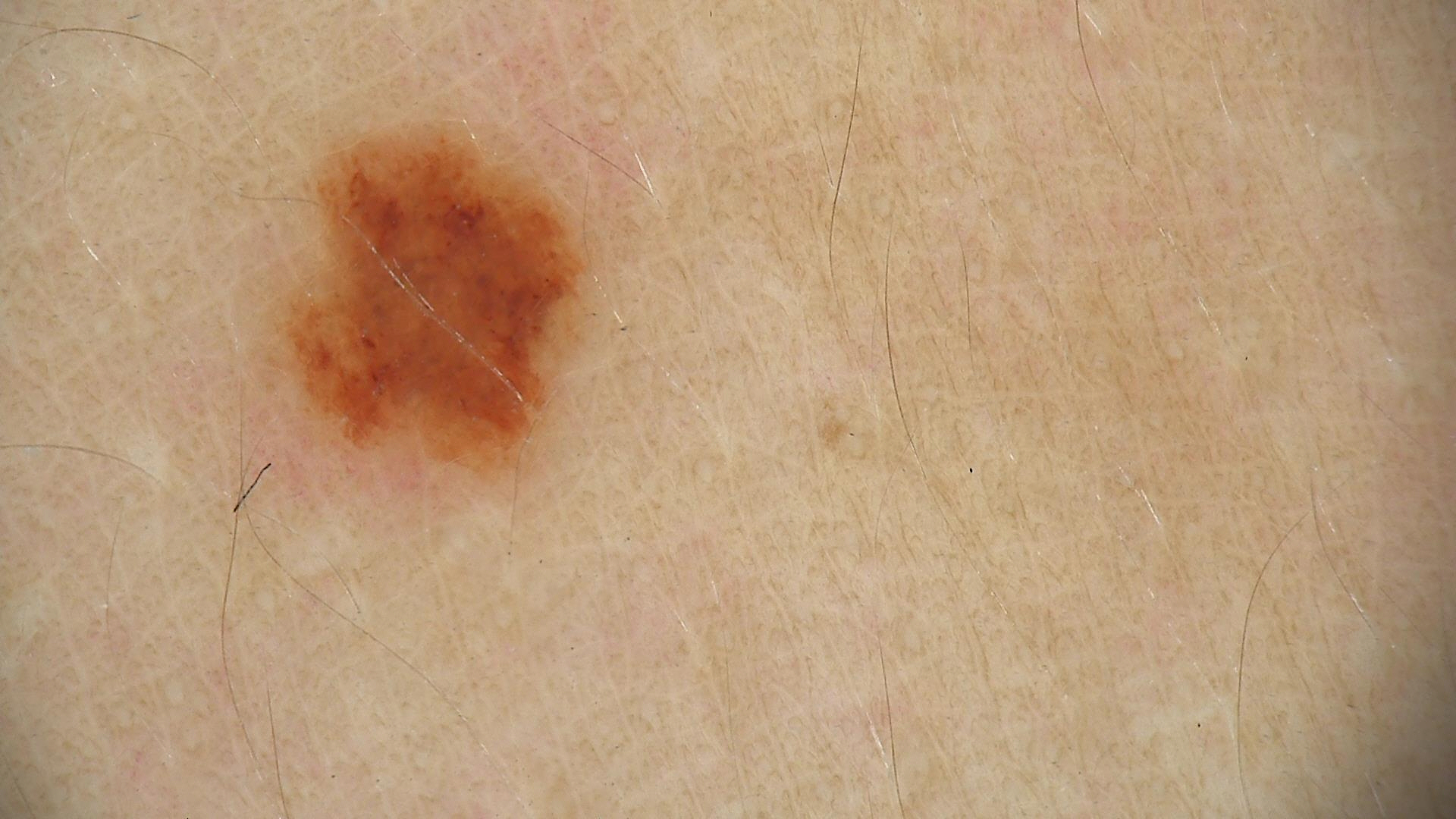A dermatoscopic image of a skin lesion.
Diagnosed as a benign lesion — a dysplastic junctional nevus.